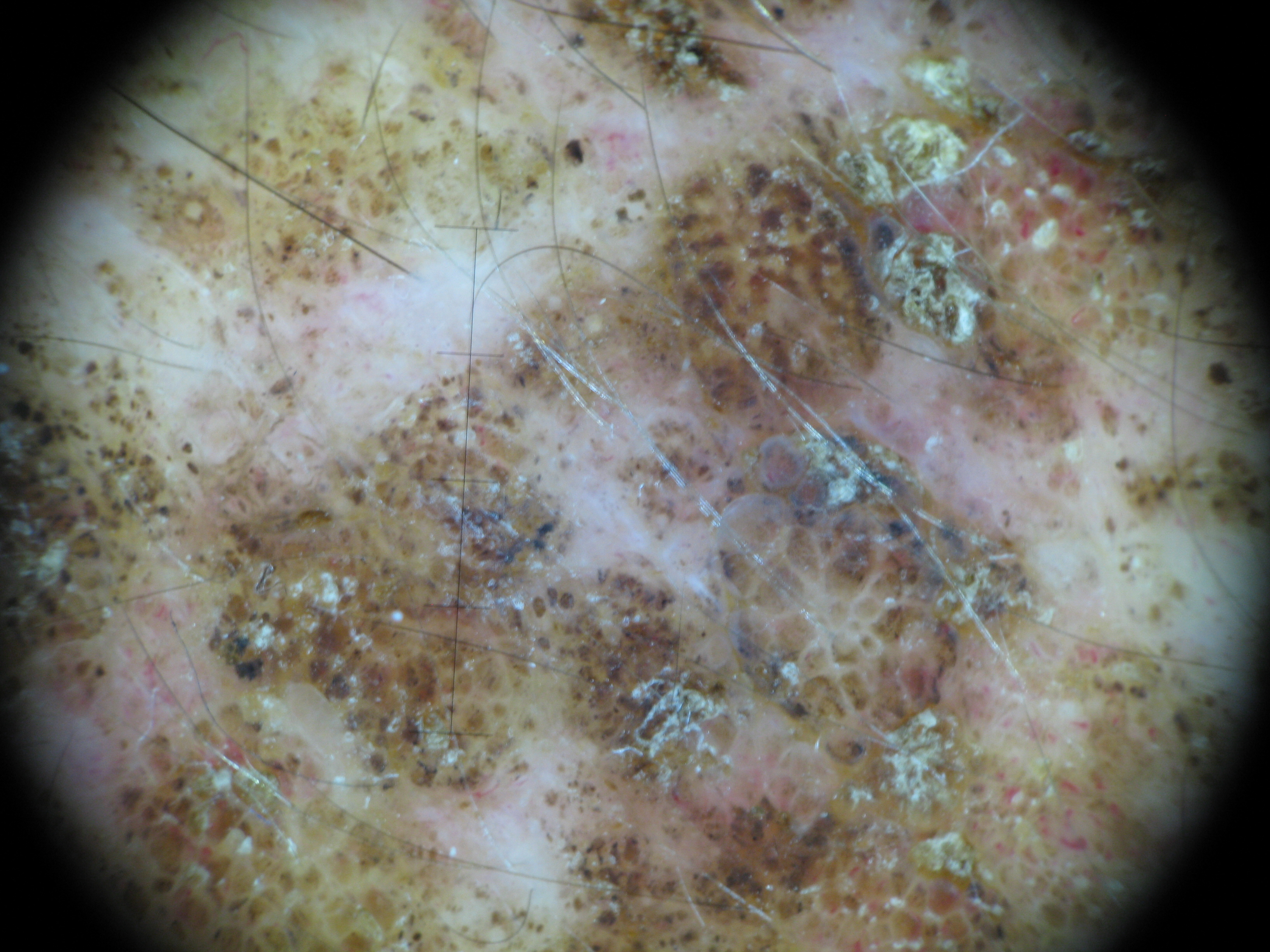Pathology: Biopsy-confirmed as a melanoma.